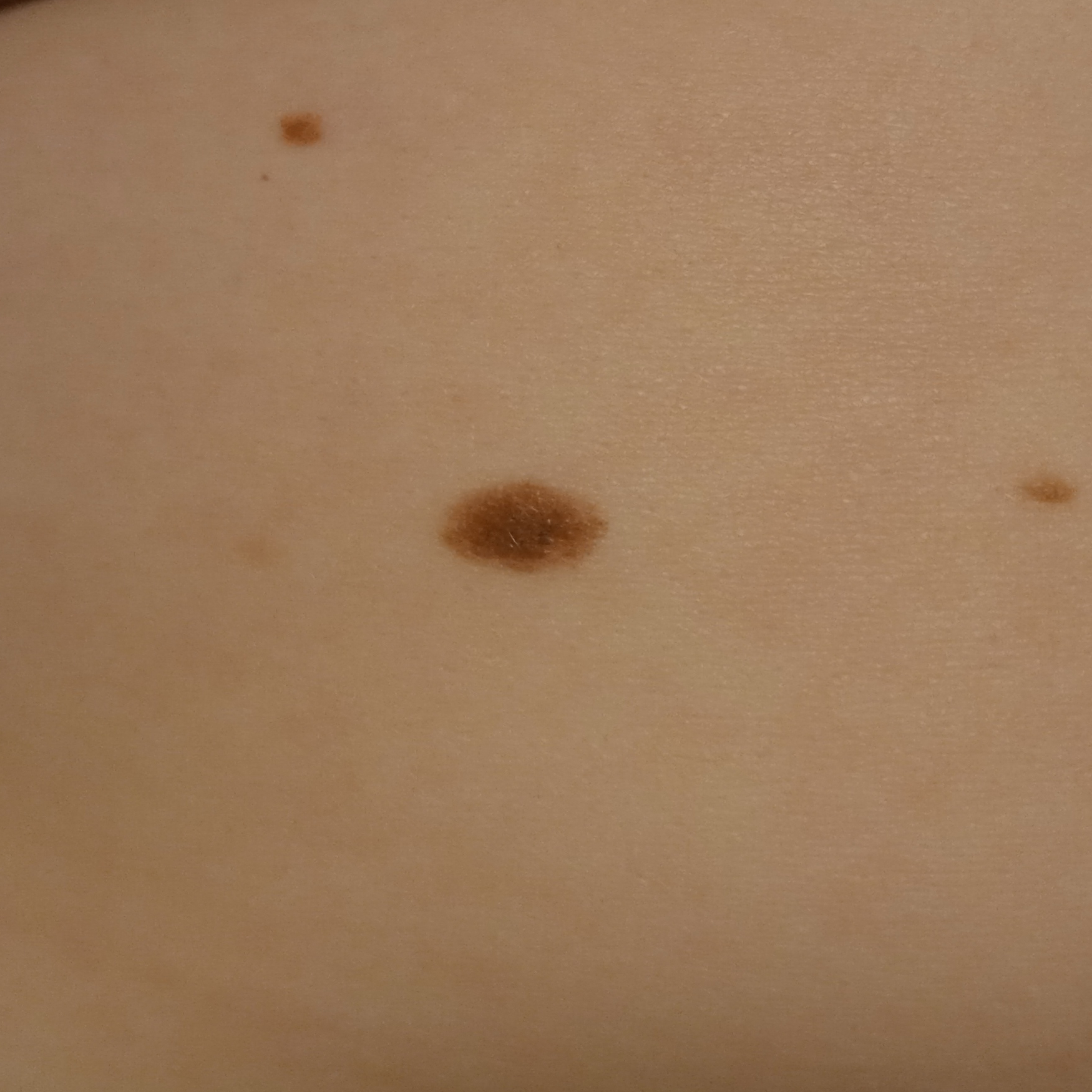{"image": "clinical photograph", "patient": {"age": 27, "sex": "female"}, "sun_reaction": "skin reddens with sun exposure", "referral": "research study (no referral diagnosis)", "lesion_location": "the back", "diagnosis": {"name": "melanocytic nevus", "malignancy": "benign"}}